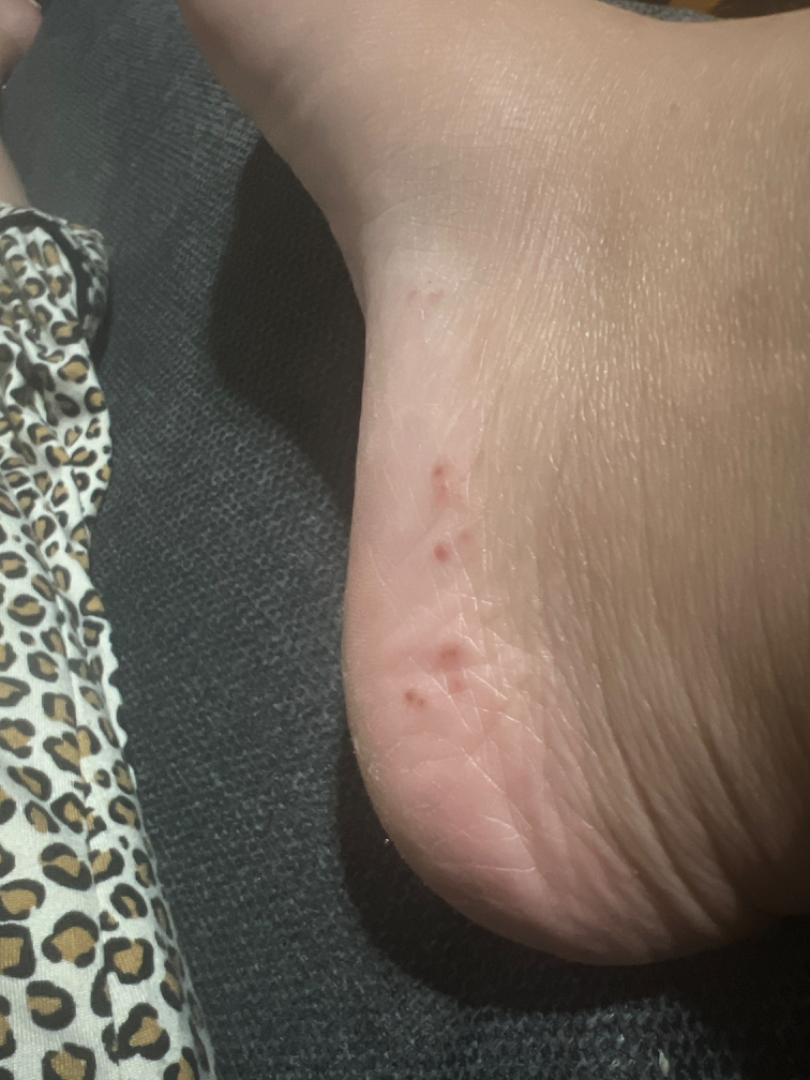Notes:
- differential · three dermatologists each reviewed the case: favoring Tinea; also consider Eczema